Close-up view, the condition has been present for less than one week, the lesion involves the back of the hand and arm, the lesion is described as raised or bumpy — 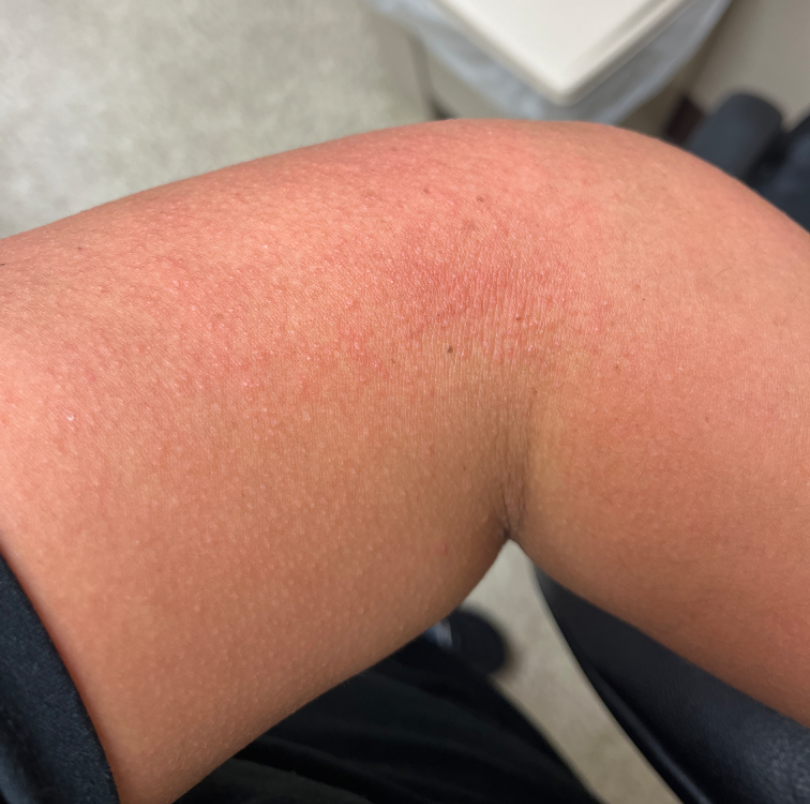Notes:
* dermatologist impression · single-reviewer assessment: Eczema and Acute and chronic dermatitis were each considered, in no particular order